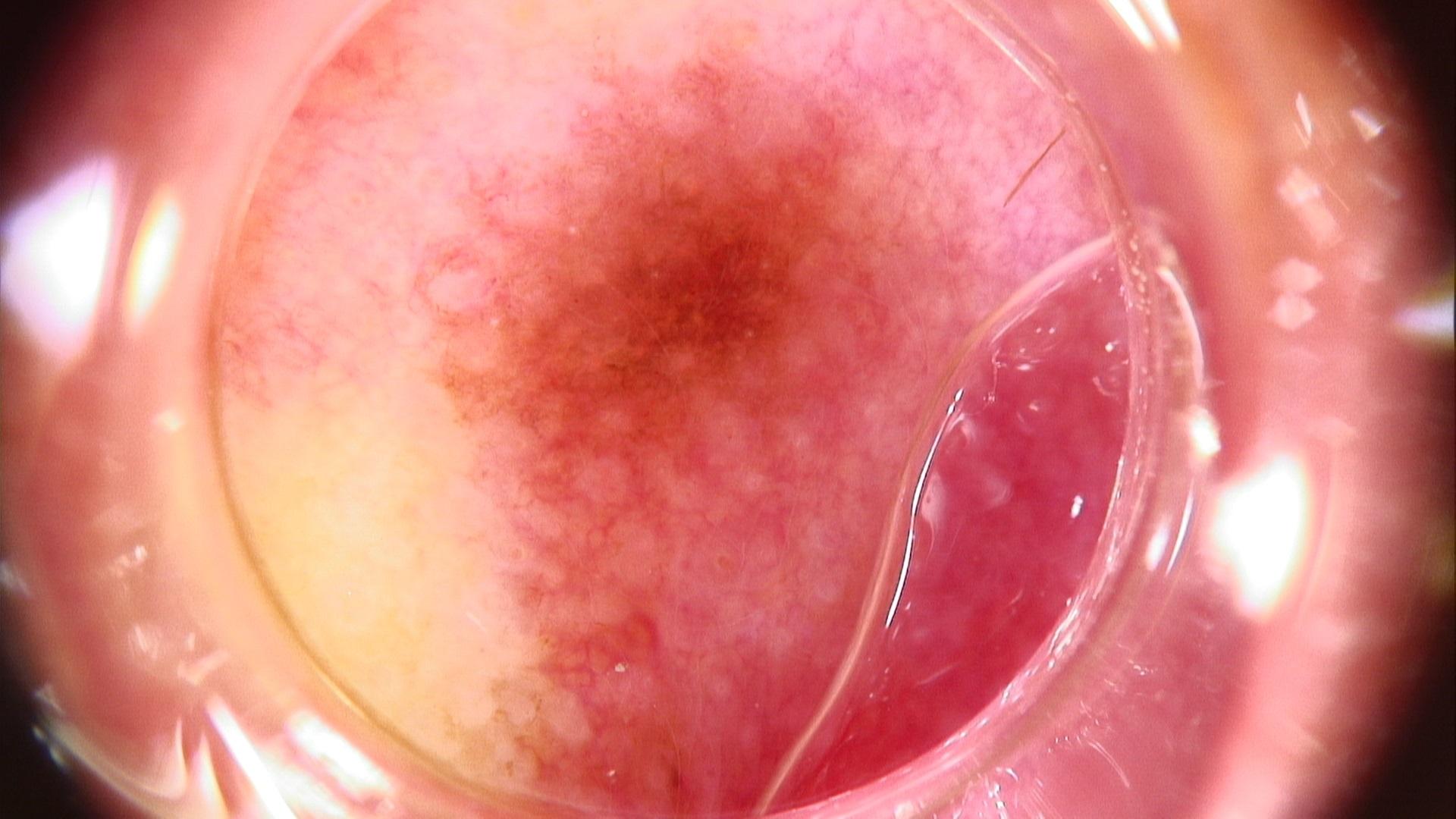The chart documents melanoma in a first-degree relative. A dermoscopic photograph of a skin lesion. A male patient about 40 years old. The lesion is on the head or neck. The diagnostic impression was a melanocytic lesion — a nevus.